The patient says their skin reddens with sun exposure; collected as part of a research study, without a referral diagnosis; a skin lesion imaged with a dermatoscope: 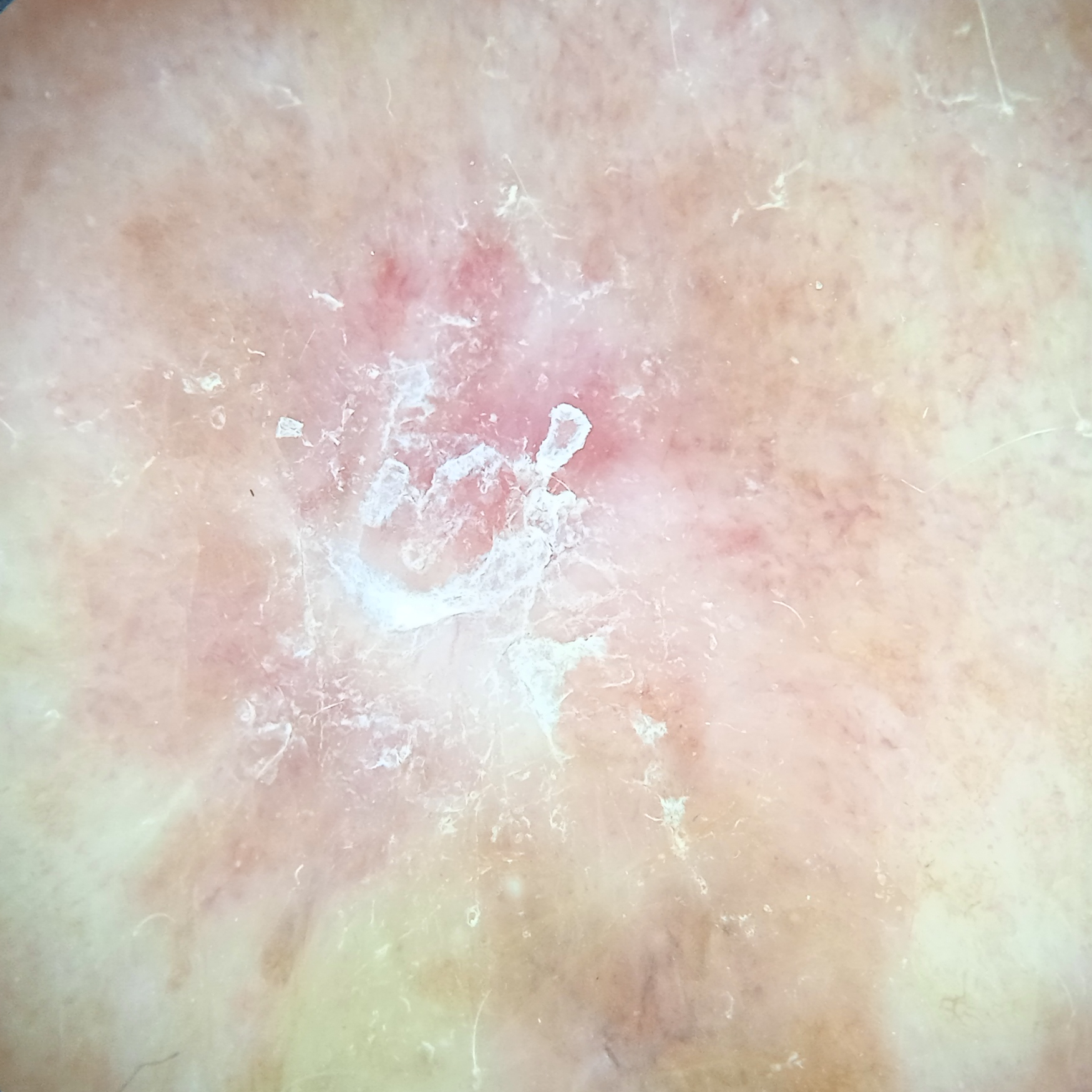Located on the back. The consensus diagnosis for this lesion was a squamous cell carcinoma.